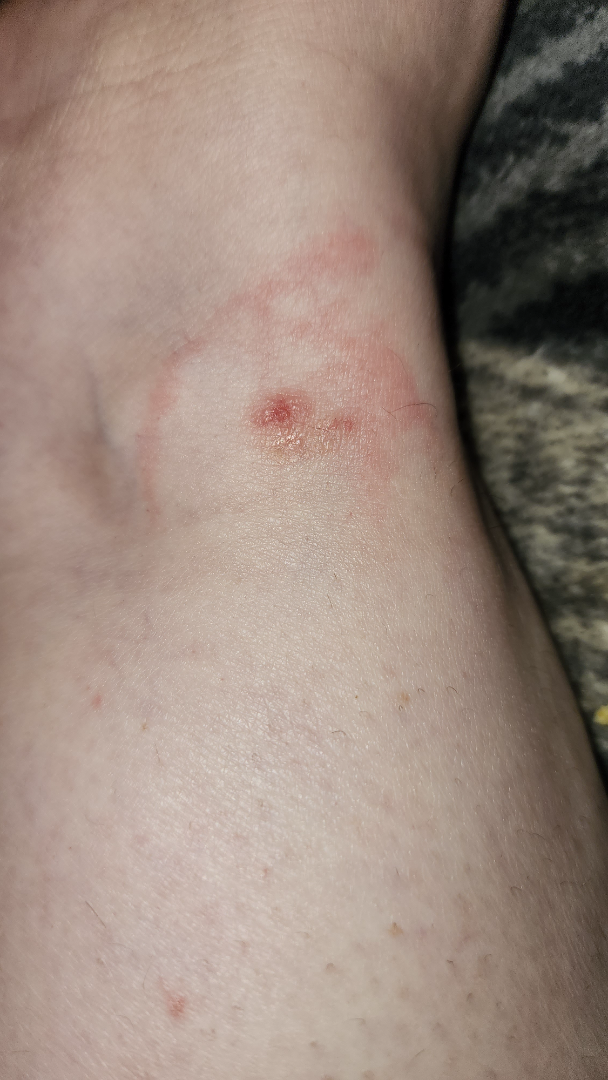Q: Anatomic location?
A: top or side of the foot
Q: Image view?
A: close-up
Q: Who is the patient?
A: female, age 40–49
Q: What is the differential diagnosis?
A: Insect Bite (primary); Allergic Contact Dermatitis (considered); Urticaria (unlikely)